The contributor reports the lesion is raised or bumpy. The lesion is associated with itching and bothersome appearance. Self-categorized by the patient as a rash. The affected area is the arm and leg. The contributor is a male aged 18–29. This image was taken at an angle — 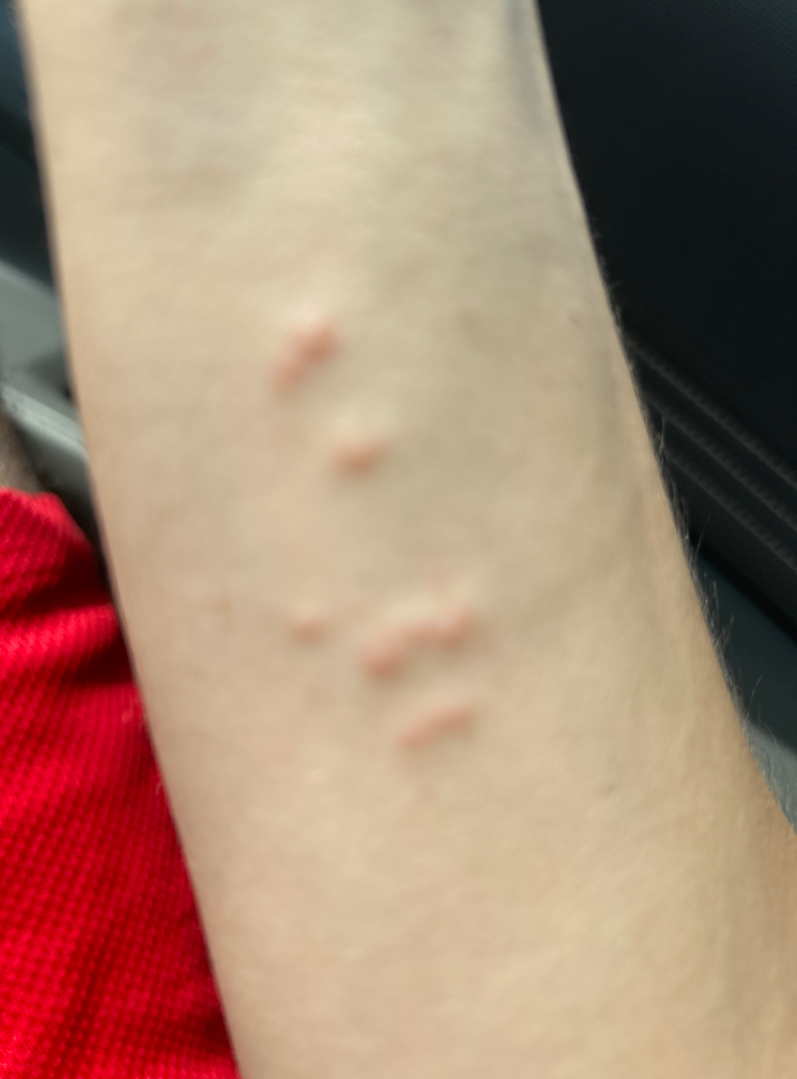Review:
The reviewing dermatologist was unable to assign a differential diagnosis from the image.